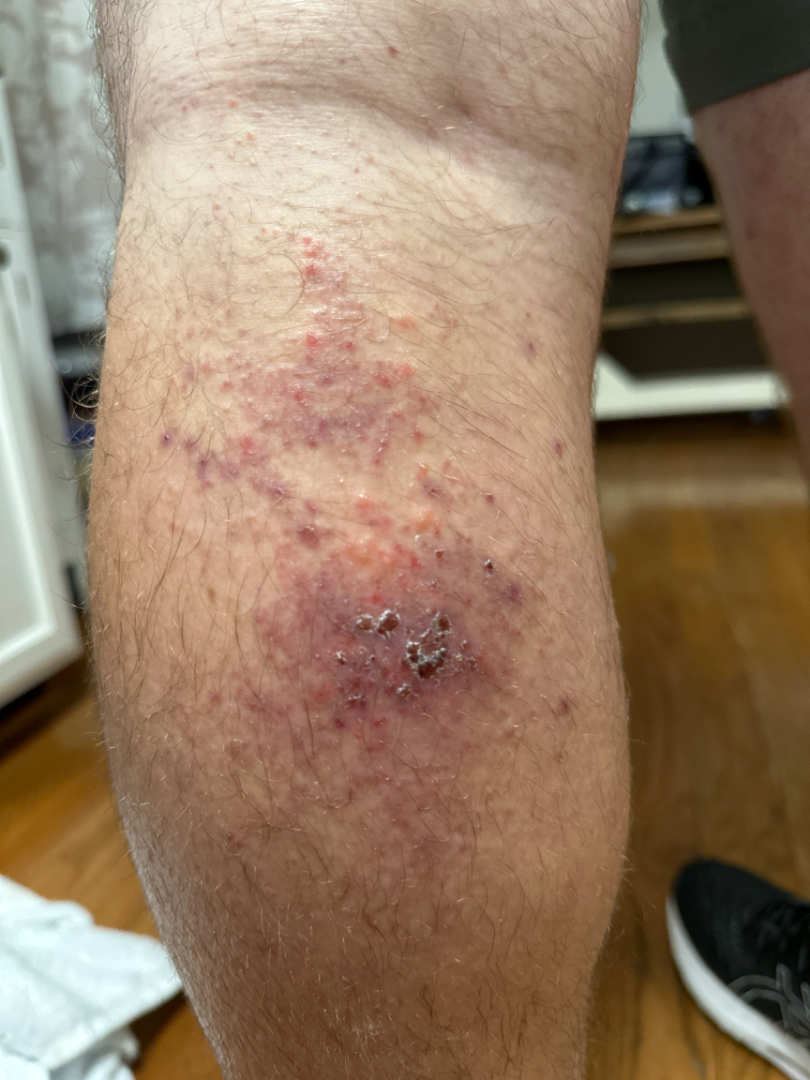The skin condition could not be confidently assessed from this image. The leg is involved. The contributor notes the lesion is raised or bumpy. The lesion is associated with itching, bleeding, burning, enlargement, pain and darkening. The condition has been present for one to three months. This is a close-up image. The patient considered this a rash.